A male subject in their late 60s; a clinical photo of a skin lesion taken with a smartphone: 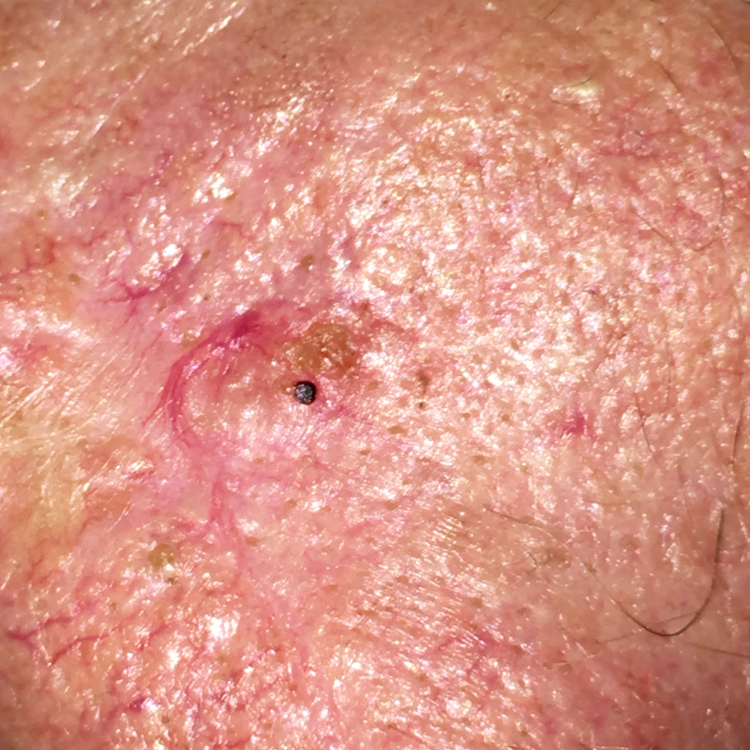| key | value |
|---|---|
| location | the face |
| diagnosis | basal cell carcinoma (biopsy-proven) |